A dermatoscopic image of a skin lesion — 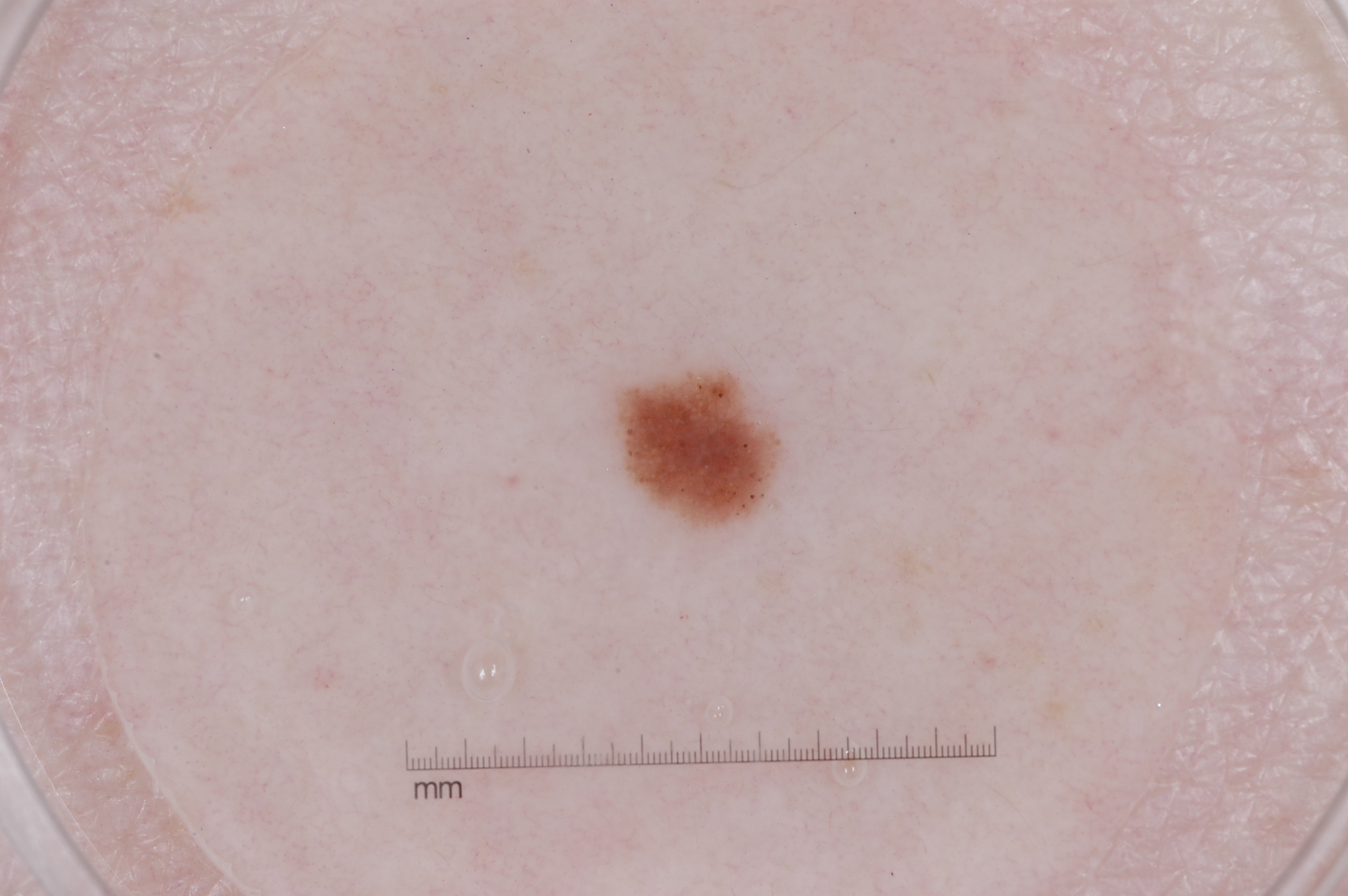In (x1, y1, x2, y2) order, the lesion occupies the region <bbox>622, 371, 779, 525</bbox>.
On dermoscopy, the lesion shows milia-like cysts.
Clinically diagnosed as a melanocytic nevus.